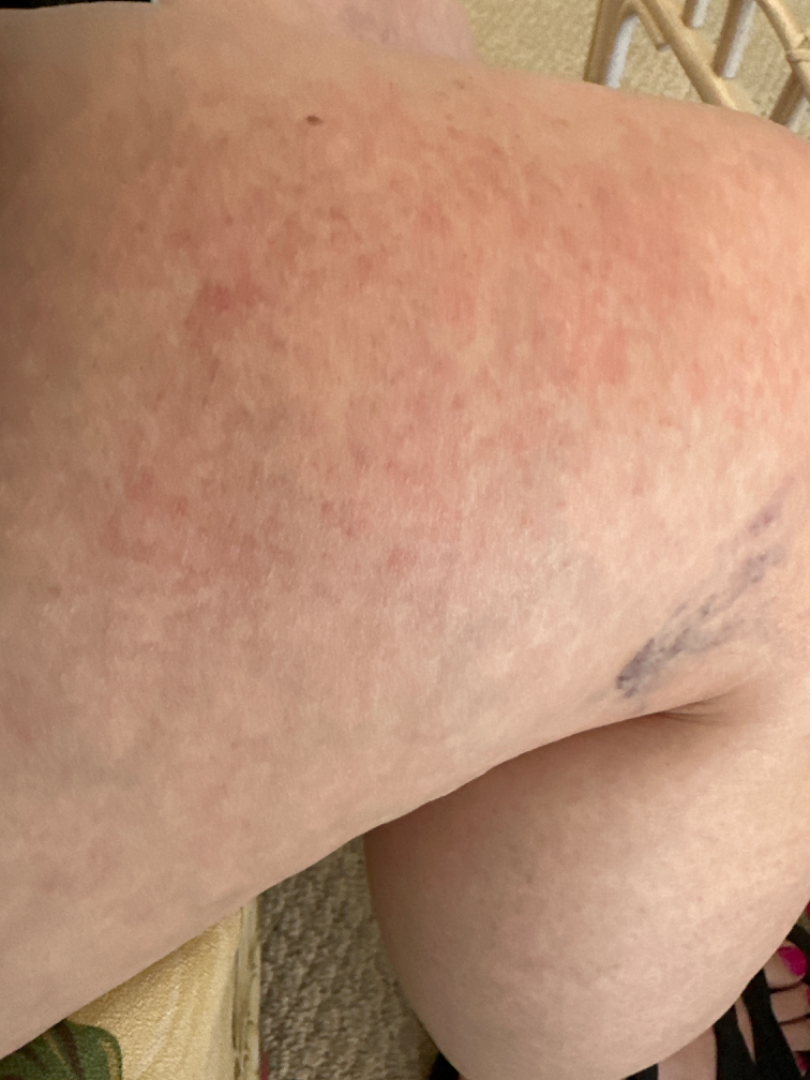Case summary:
– anatomic site: leg
– view: at an angle
– contributor: female, age 40–49
– dermatologist impression: favoring Keratosis pilaris; the differential also includes Folliculitis; an alternative is Eczema